A dermatoscopic image of a skin lesion.
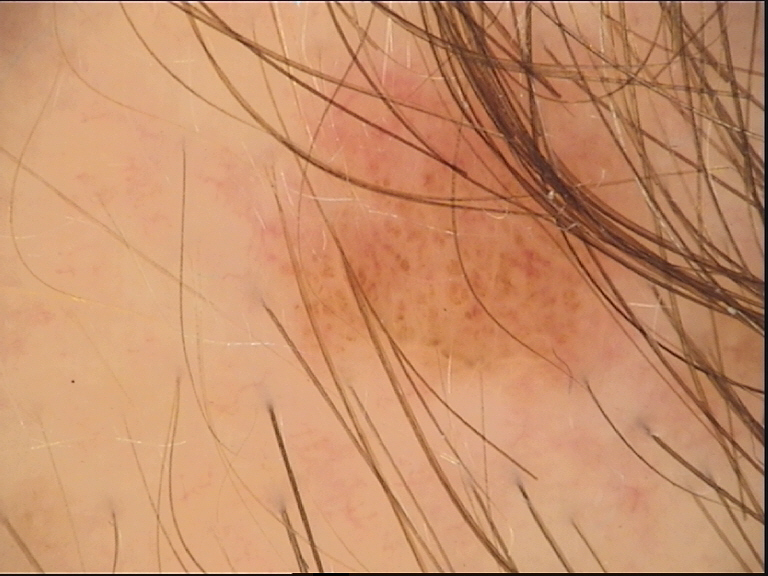Findings:
* assessment — compound nevus (expert consensus)